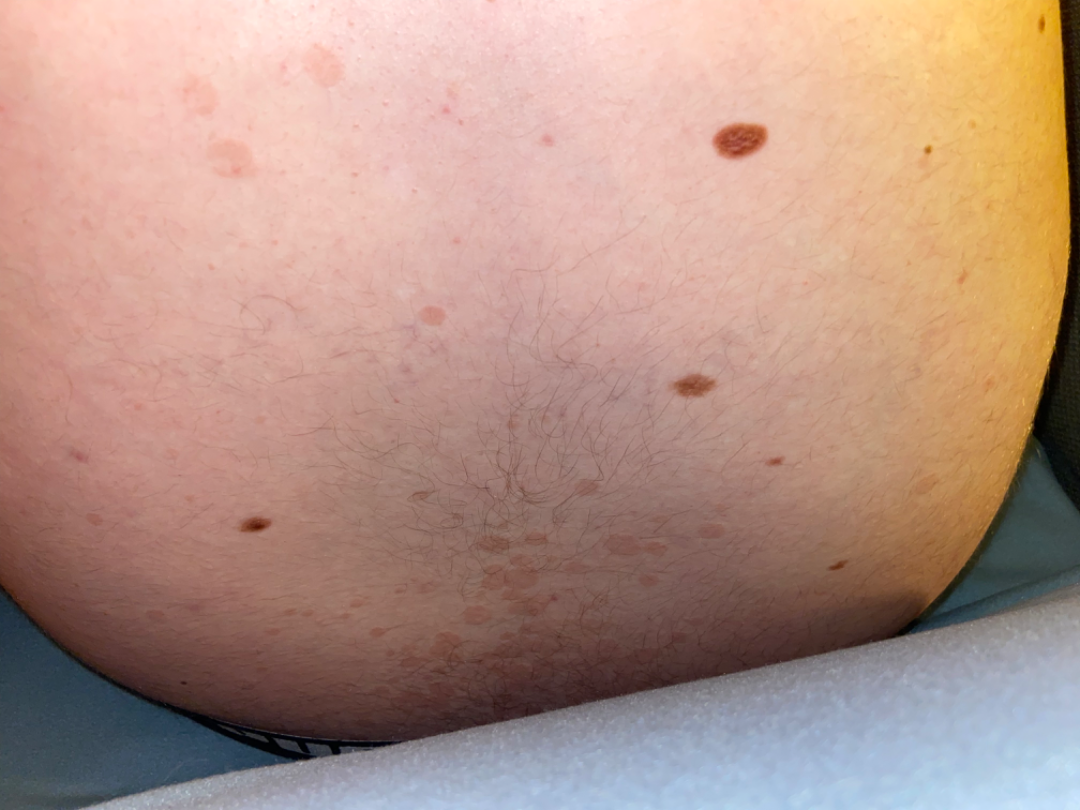The leading consideration is Tinea Versicolor.